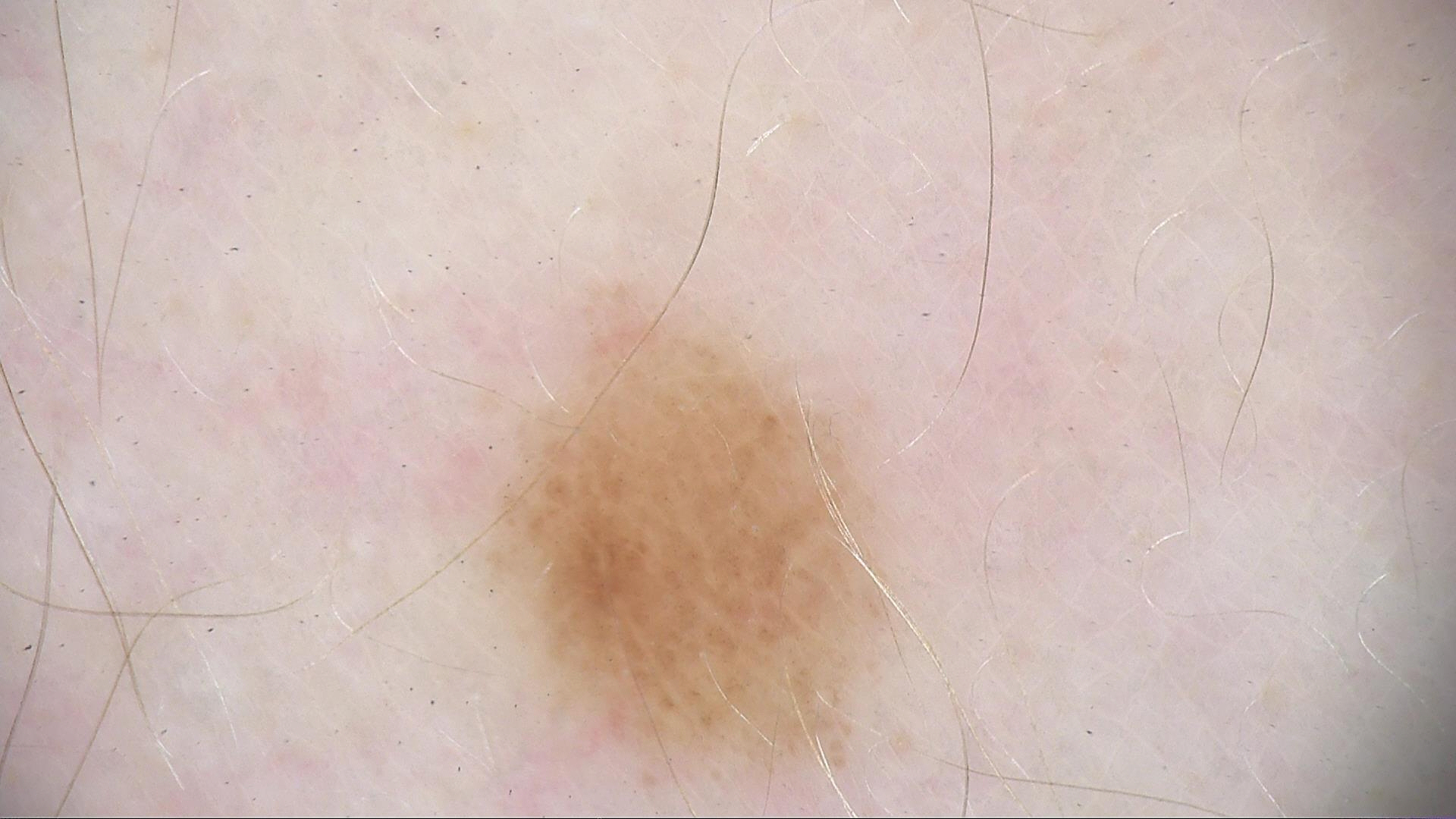Case:
– assessment: junctional nevus (expert consensus)